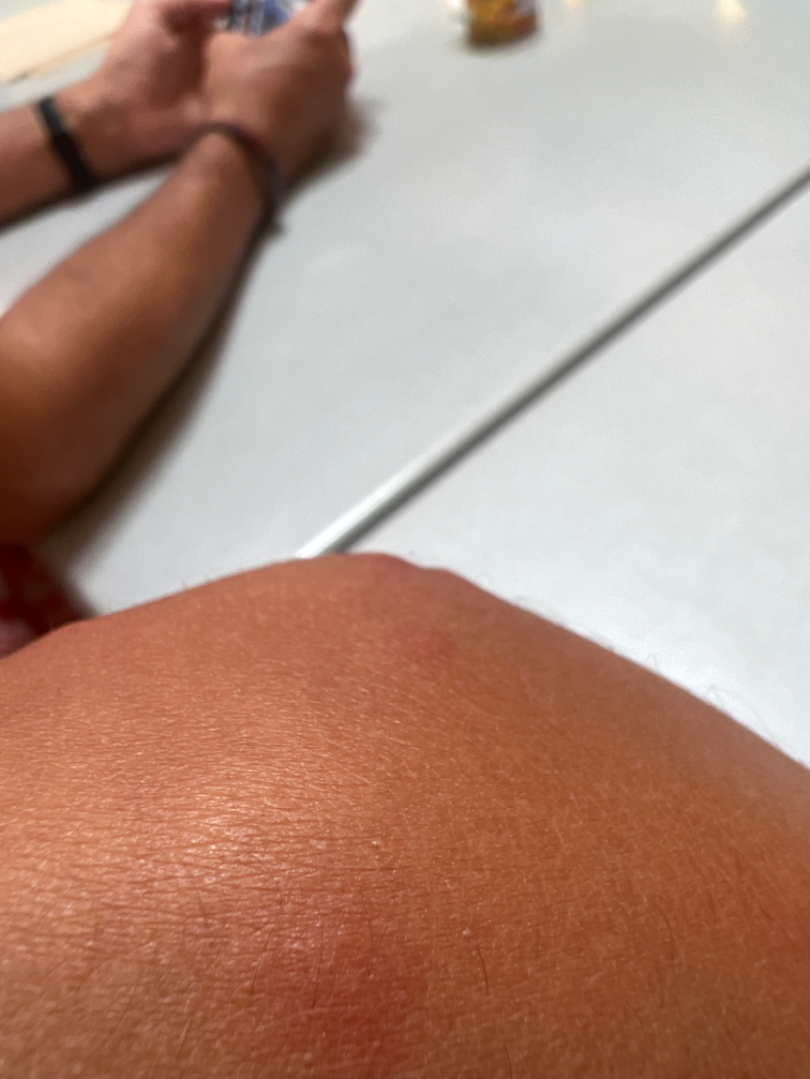Findings: The case was indeterminate on photographic review.